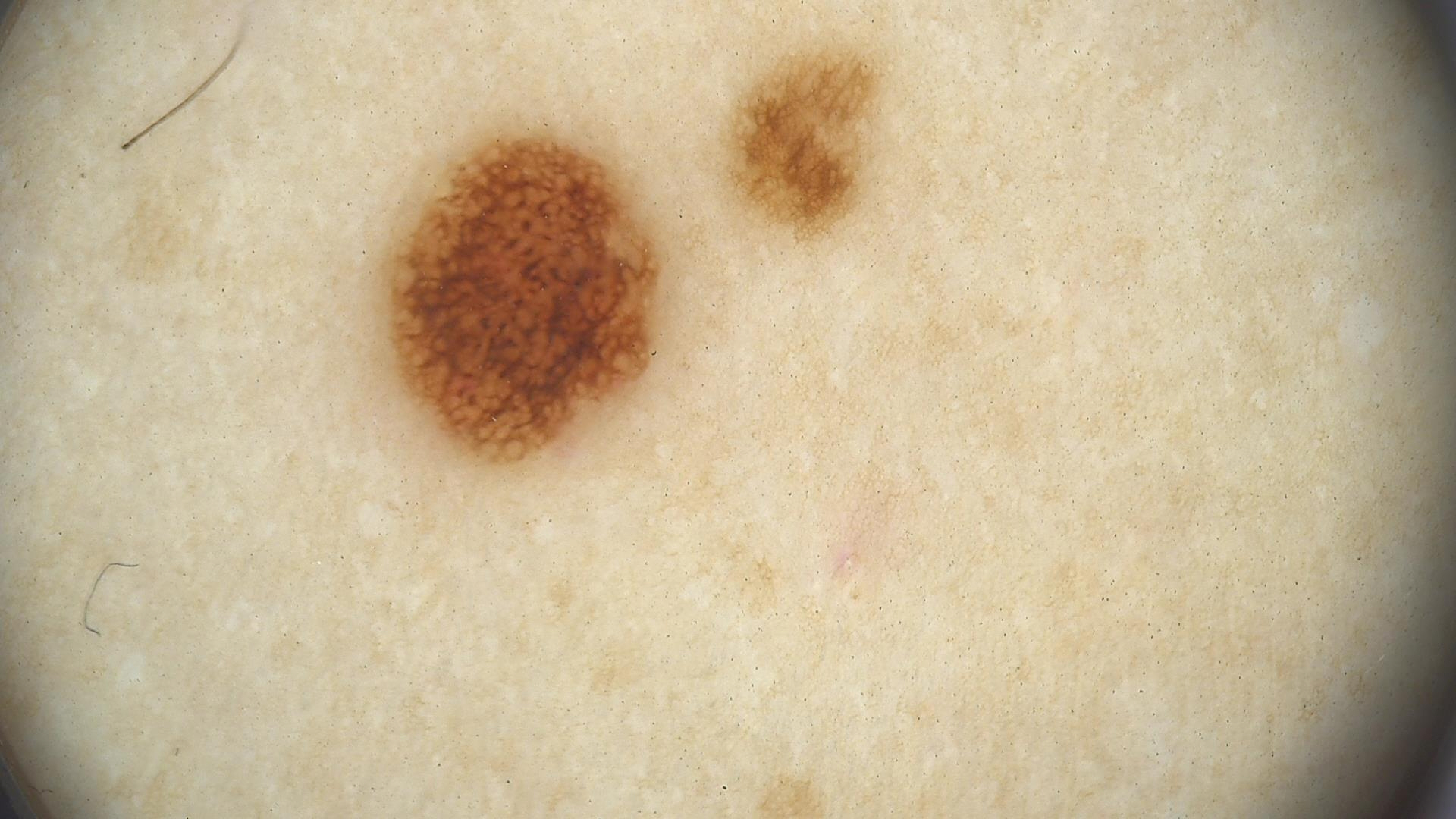Findings: A skin lesion imaged with a dermatoscope. Conclusion: Labeled as a benign lesion — a dysplastic junctional nevus.